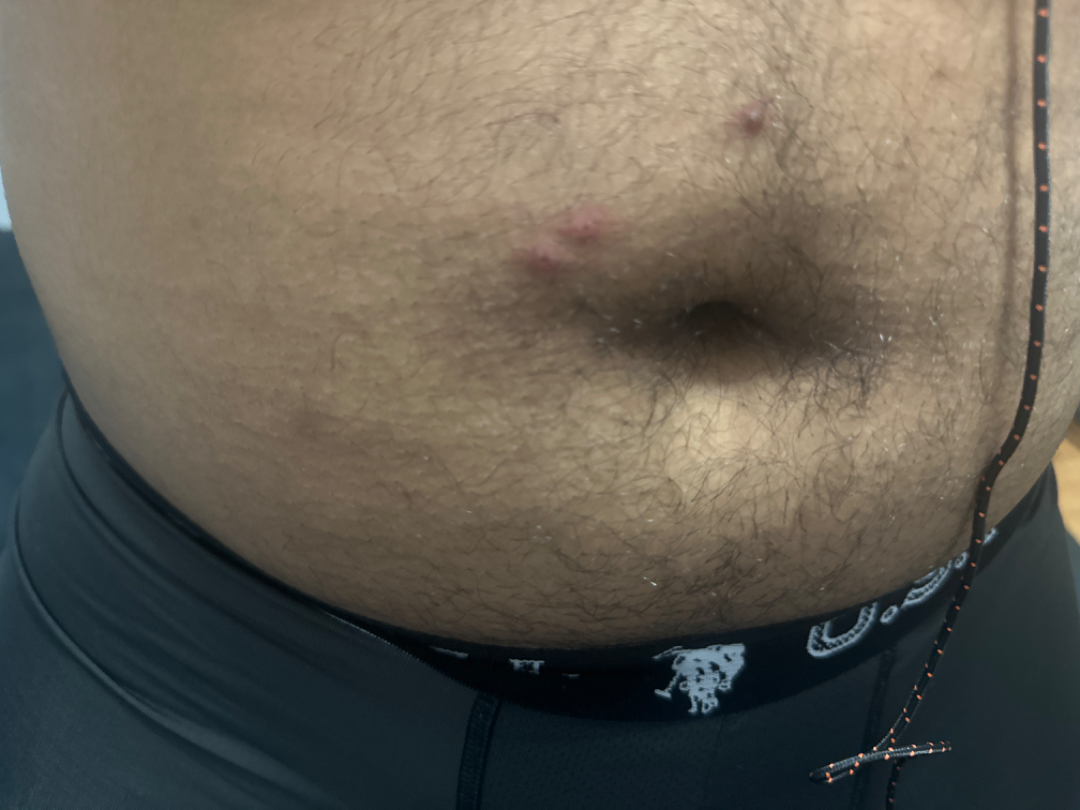– assessment: indeterminate from the photograph
– shot type: at a distance
– surface texture: fluid-filled and raised or bumpy